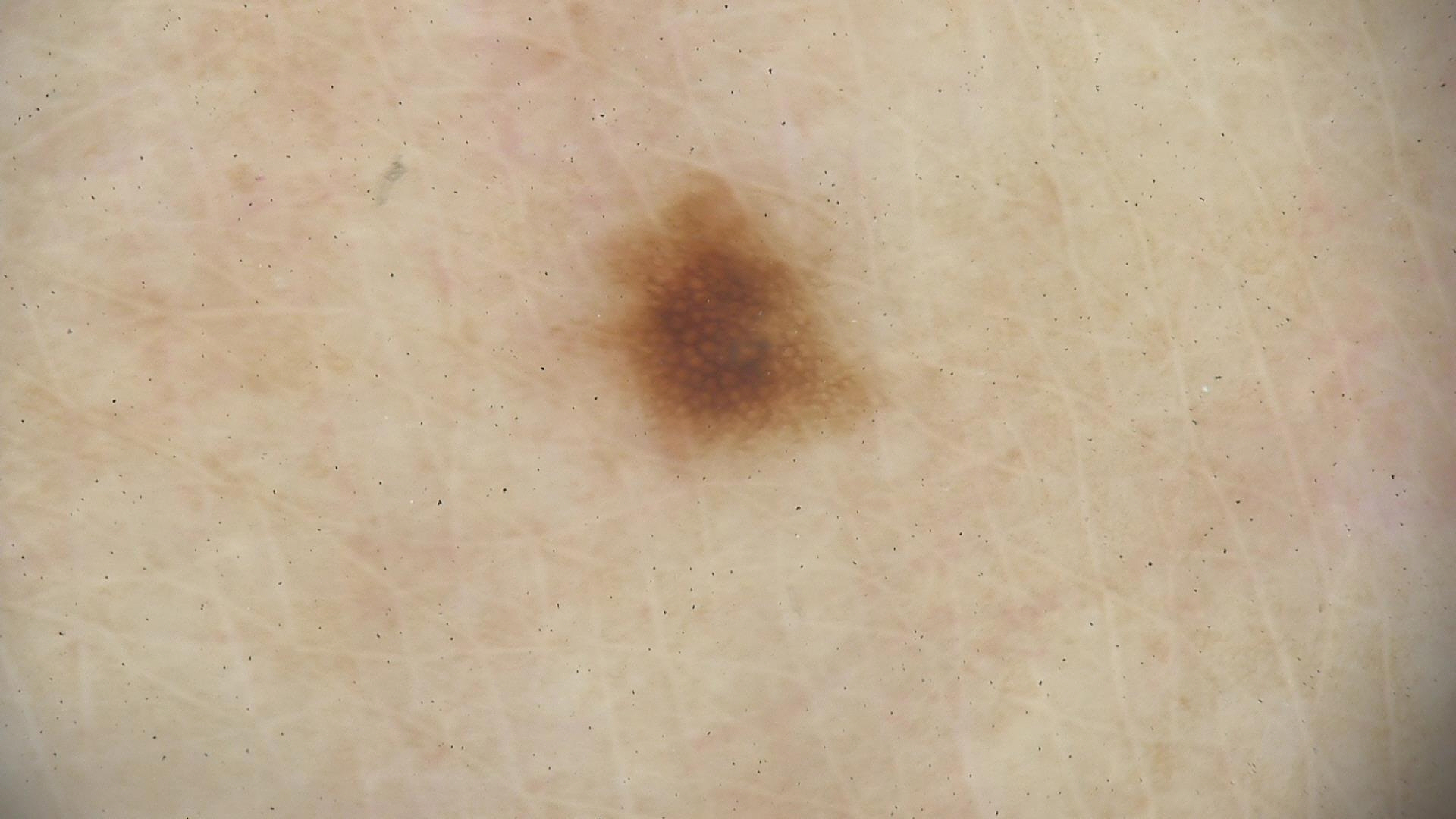Q: What is this lesion?
A: dysplastic junctional nevus (expert consensus)